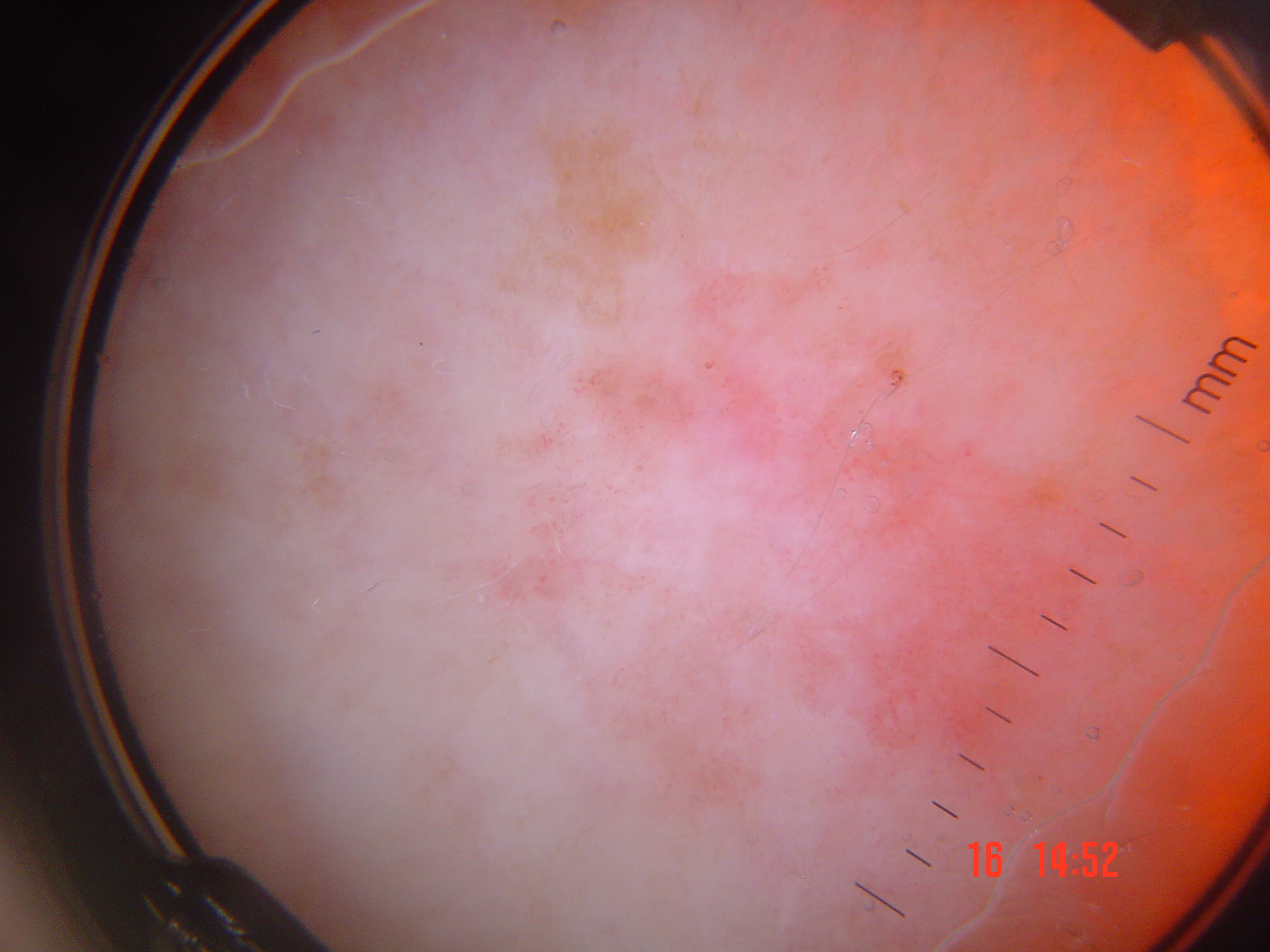A dermoscopic image of a skin lesion. Confirmed on histopathology as a malignant, keratinocytic lesion — Bowen's disease.